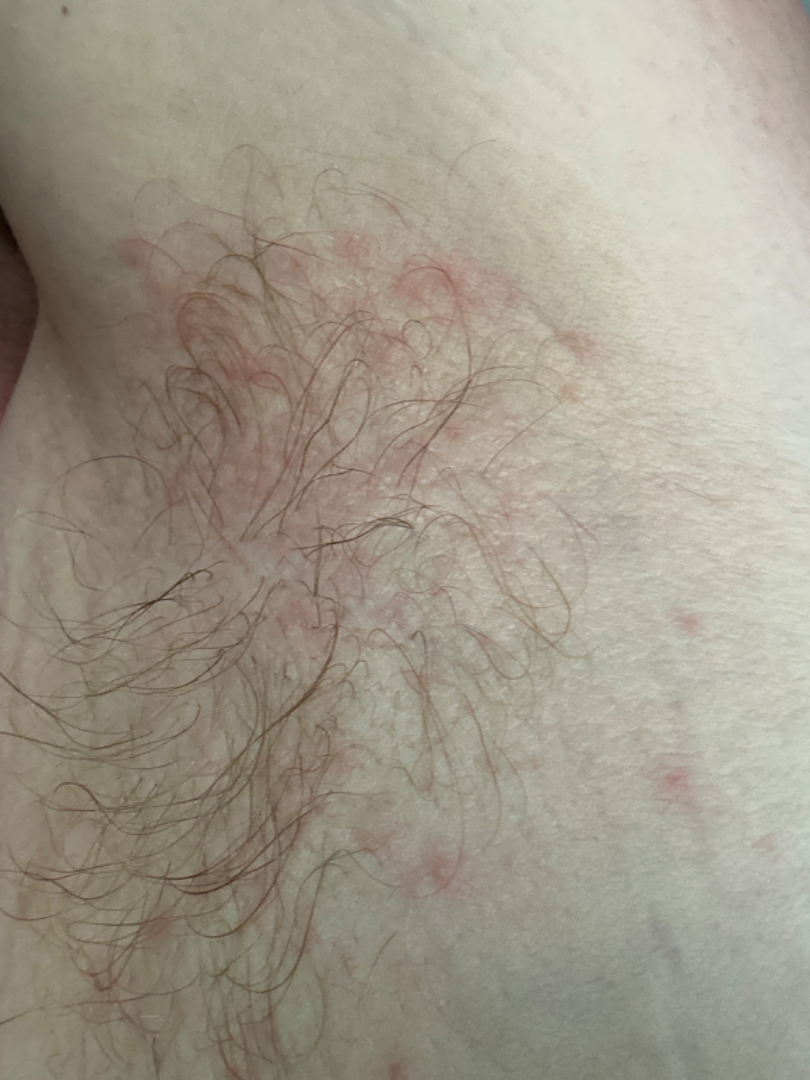Notes:
* differential: Intertrigo and Seborrheic Dermatitis were each considered, in no particular order; less probable is Folliculitis